A male patient in their late 50s · the patient was assessed as Fitzpatrick skin type II · the chart notes prior malignancy (patient or family) and pesticide exposure · a clinical close-up photograph of a skin lesion — 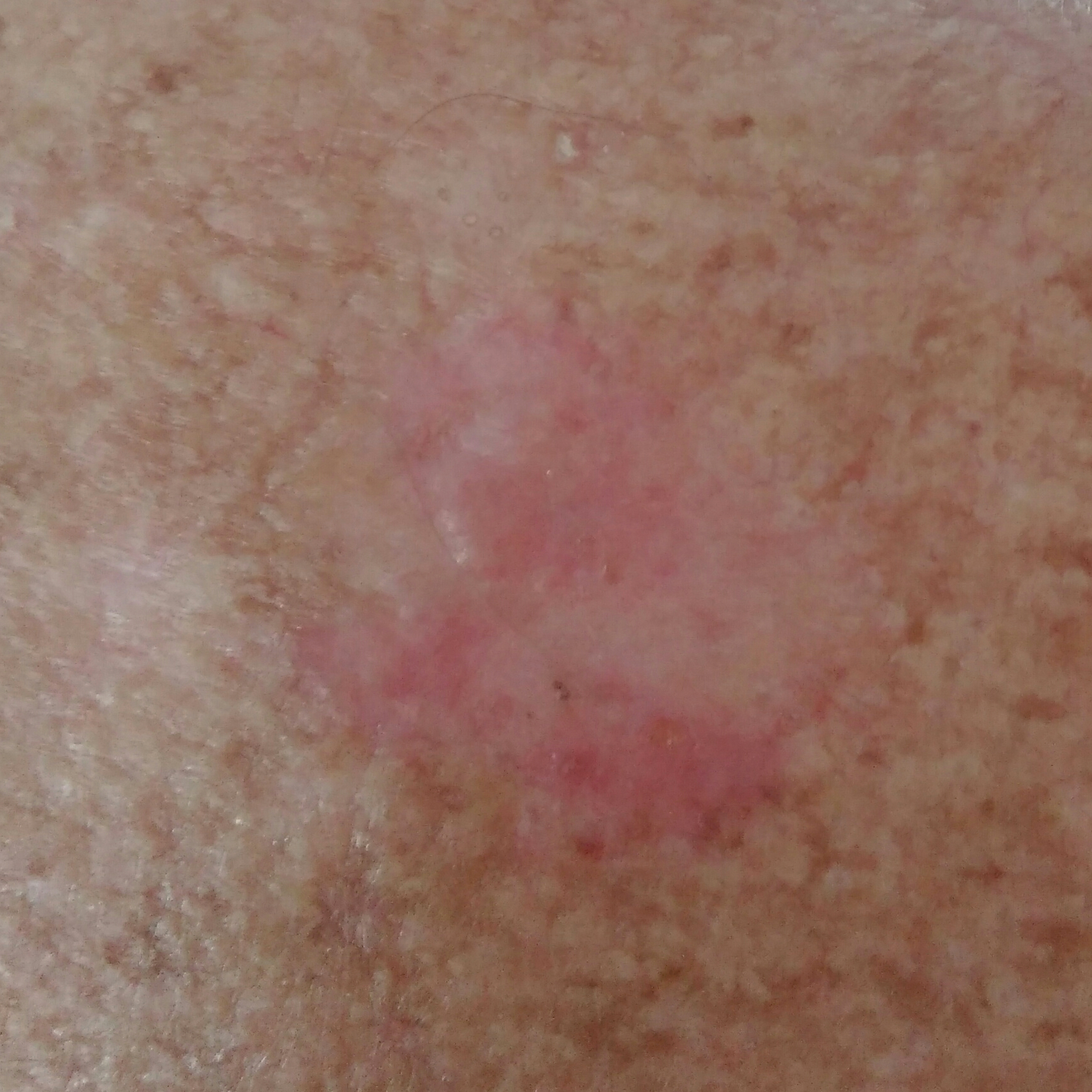Case summary: The lesion was found on the back. The lesion is roughly 21 by 20 mm. By the patient's account, the lesion itches, but has not grown and has not bled. Diagnosis: Histopathology confirmed a basal cell carcinoma.